Dermoscopy of a skin lesion.
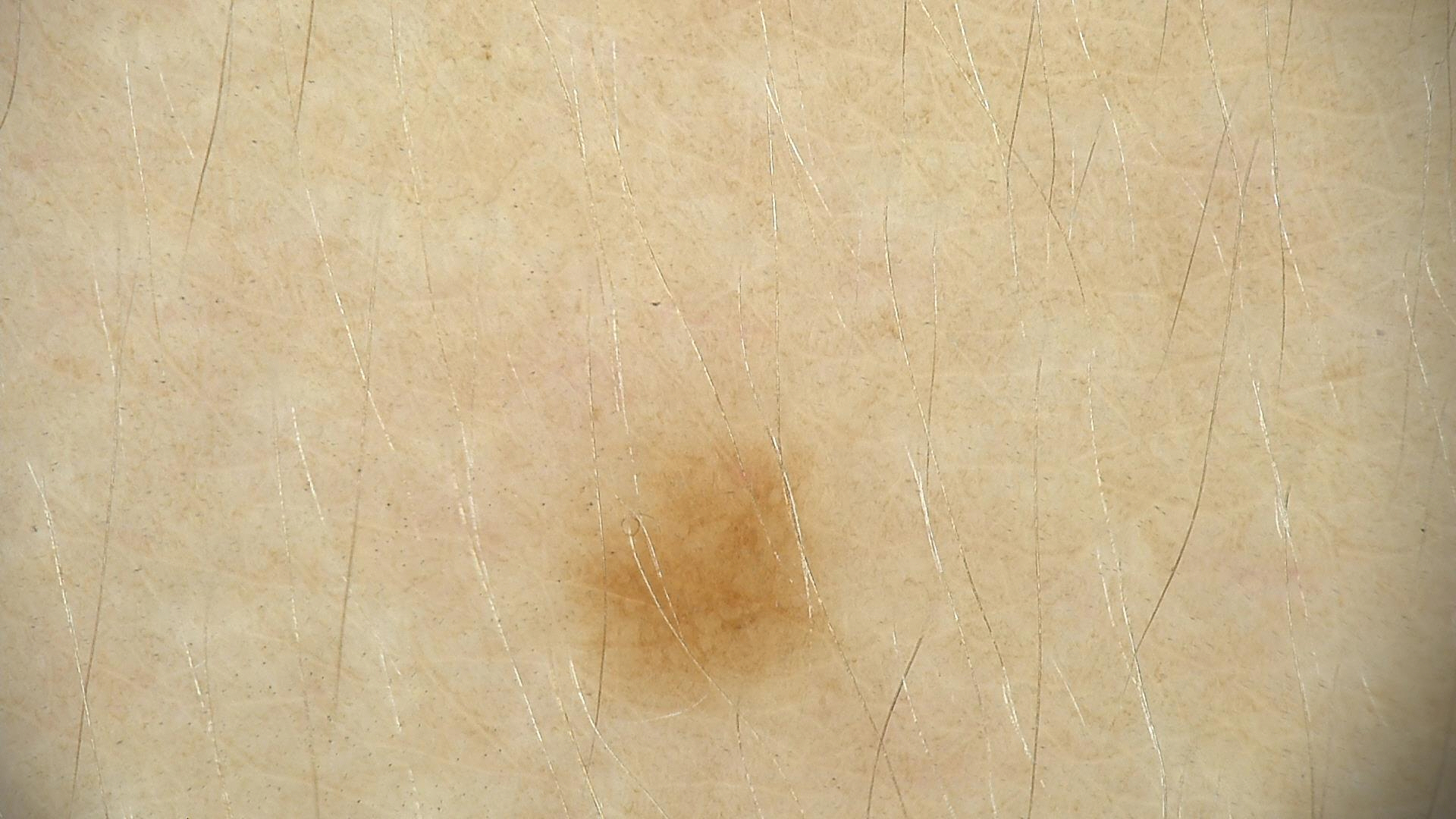The diagnostic label was a benign lesion — a dysplastic junctional nevus.